A skin lesion imaged with a dermatoscope:
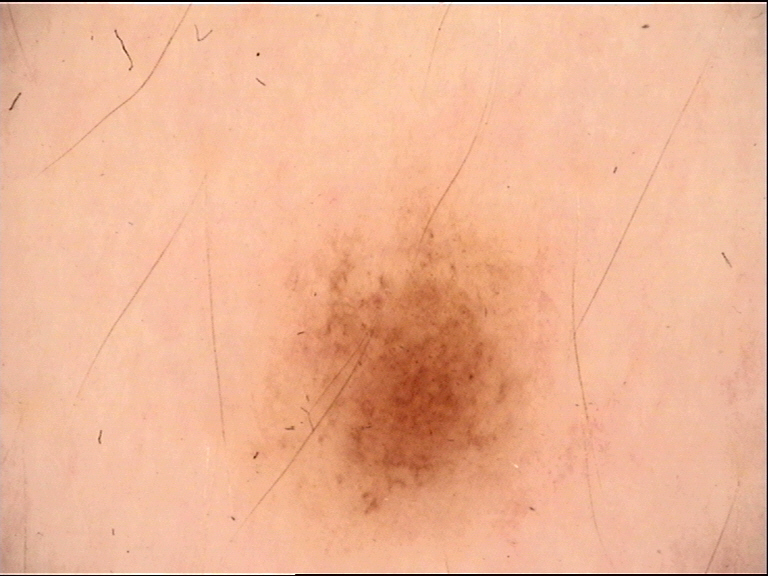diagnosis: dysplastic junctional nevus (expert consensus).